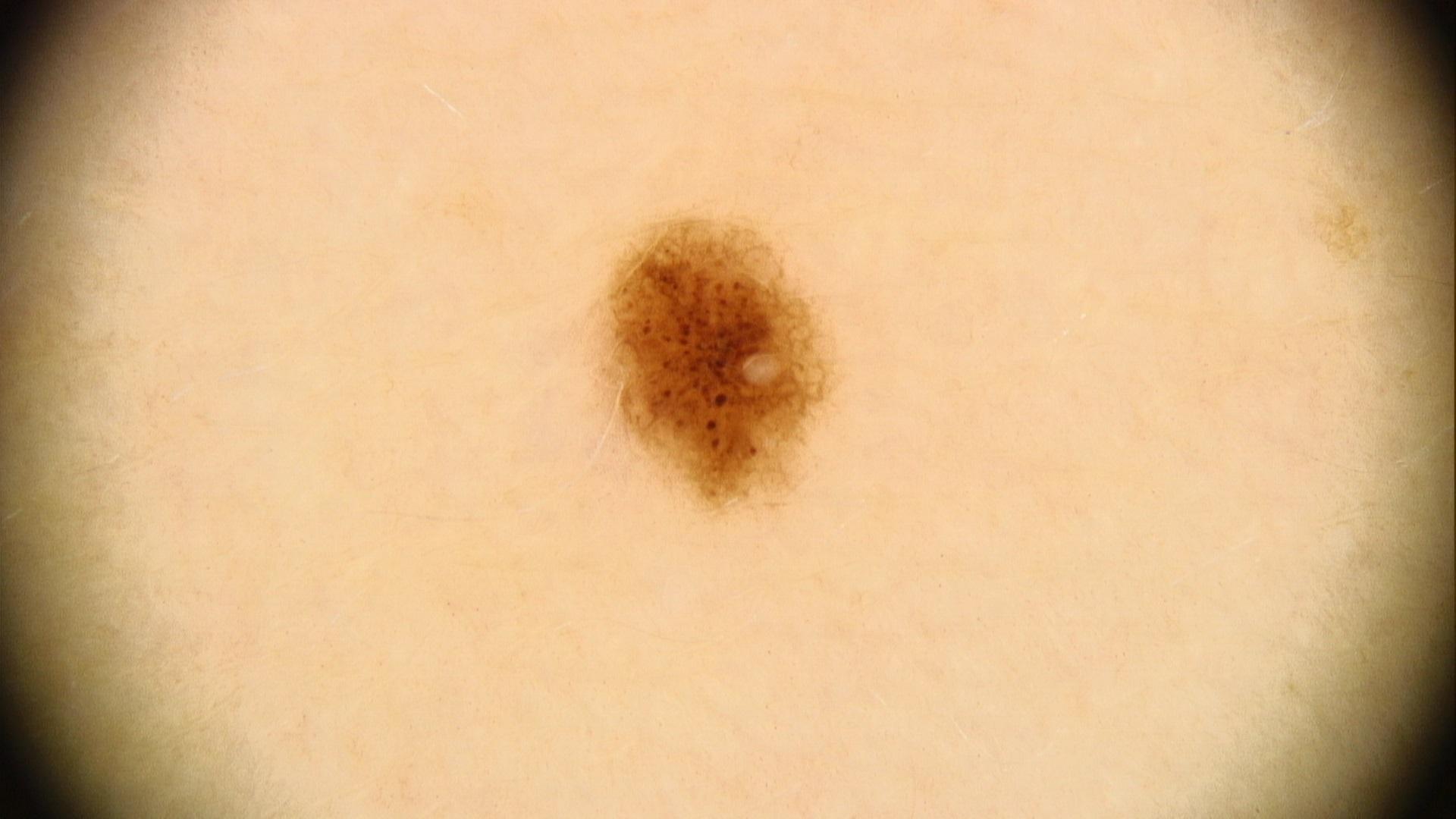Findings:
Dermoscopy of a skin lesion. A male patient approximately 40 years of age. The chart records a first-degree relative with melanoma. The patient was assessed as skin type III. The lesion was found on the trunk (the anterior trunk).
Impression:
Consistent with a lesion of melanocytic lineage — a nevus.